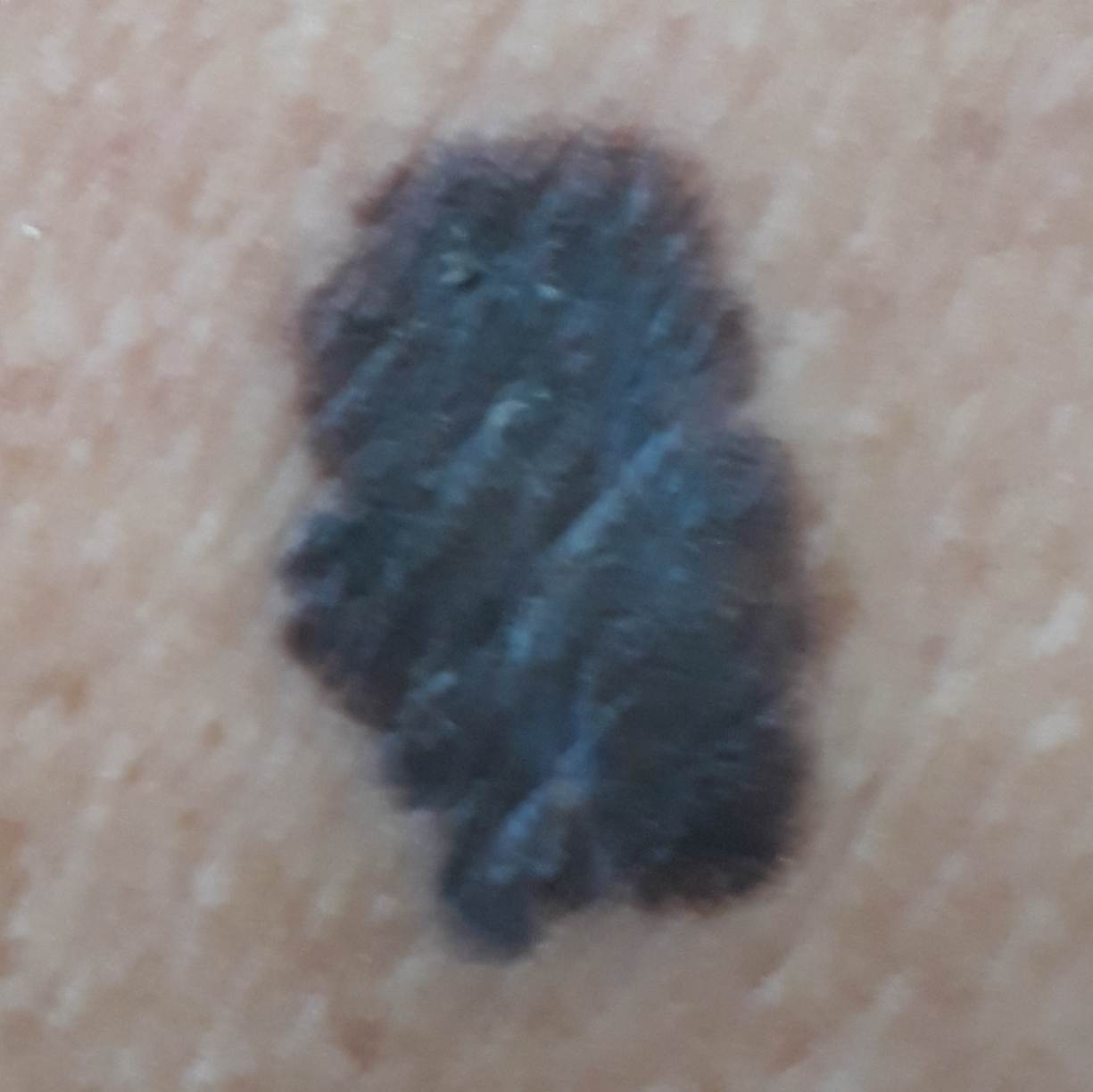A smartphone photograph of a skin lesion.
The chart records no prior malignancy (patient or family).
A male patient 58 years old.
The lesion measures approximately 18 × 12 mm.
Histopathology confirmed a melanoma.